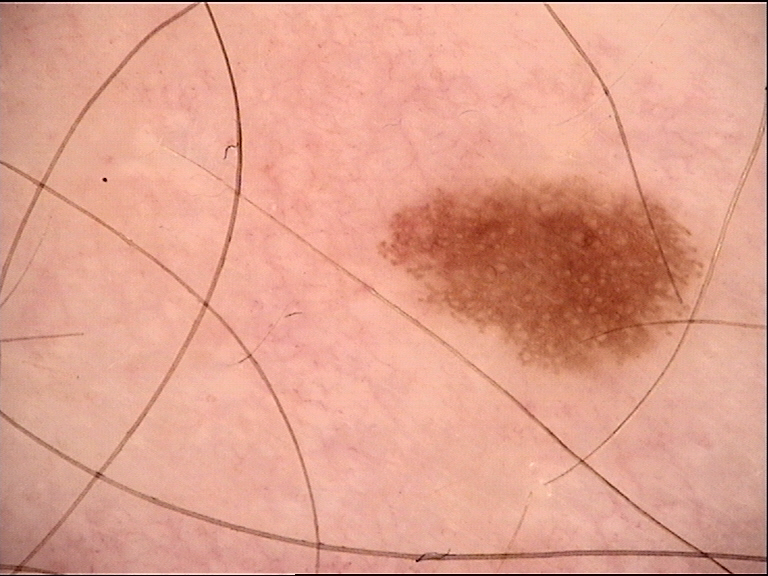diagnosis: dysplastic junctional nevus (expert consensus).